A skin lesion imaged with a dermatoscope.
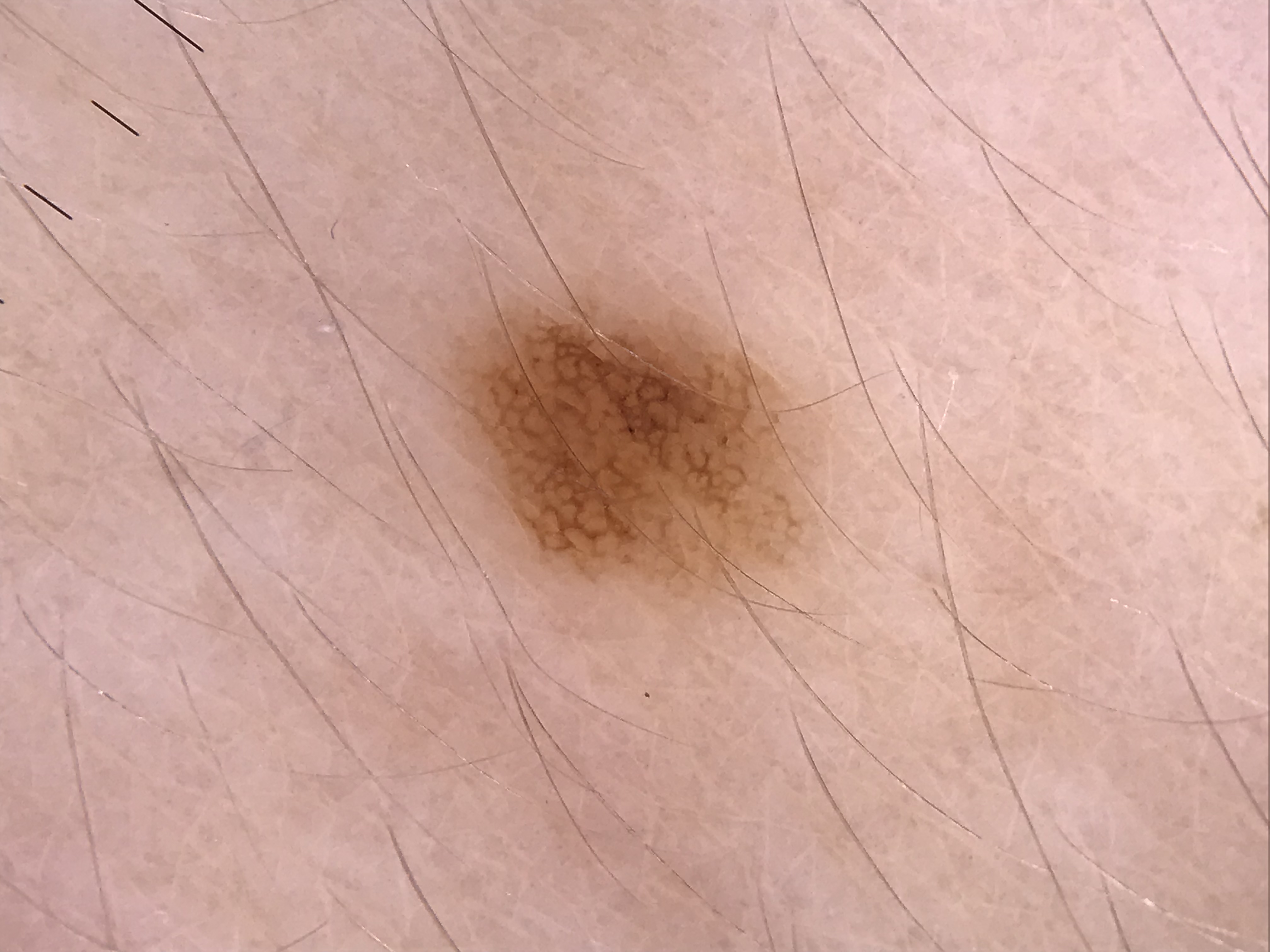This is a banal lesion. Classified as a junctional nevus.